A dermoscopy image of a single skin lesion.
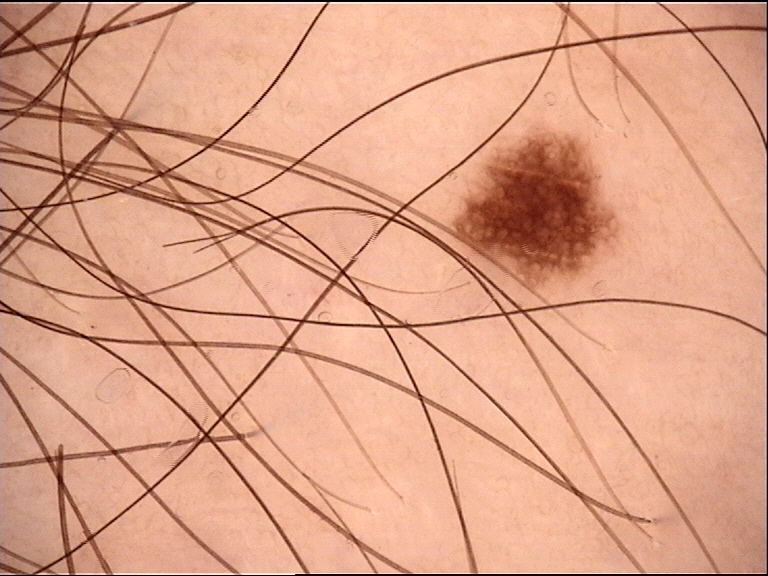class: dysplastic junctional nevus (expert consensus).